The front of the torso is involved. The condition has been present for about one day. Self-categorized by the patient as a rash. Fitzpatrick I; human graders estimated Monk Skin Tone 2–3. Texture is reported as raised or bumpy. Reported lesion symptoms include burning, enlargement and itching. This is a close-up image:
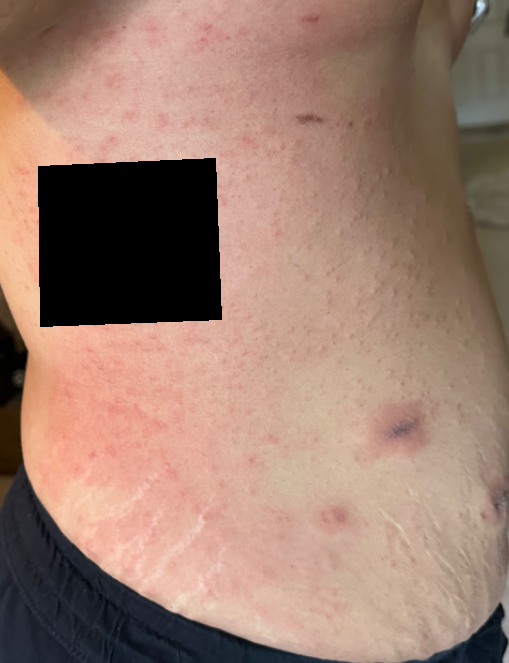Notes:
* assessment · most likely Hypersensitivity